The photograph is a close-up of the affected area; the lesion involves the back of the torso, arm, leg, head or neck and front of the torso:
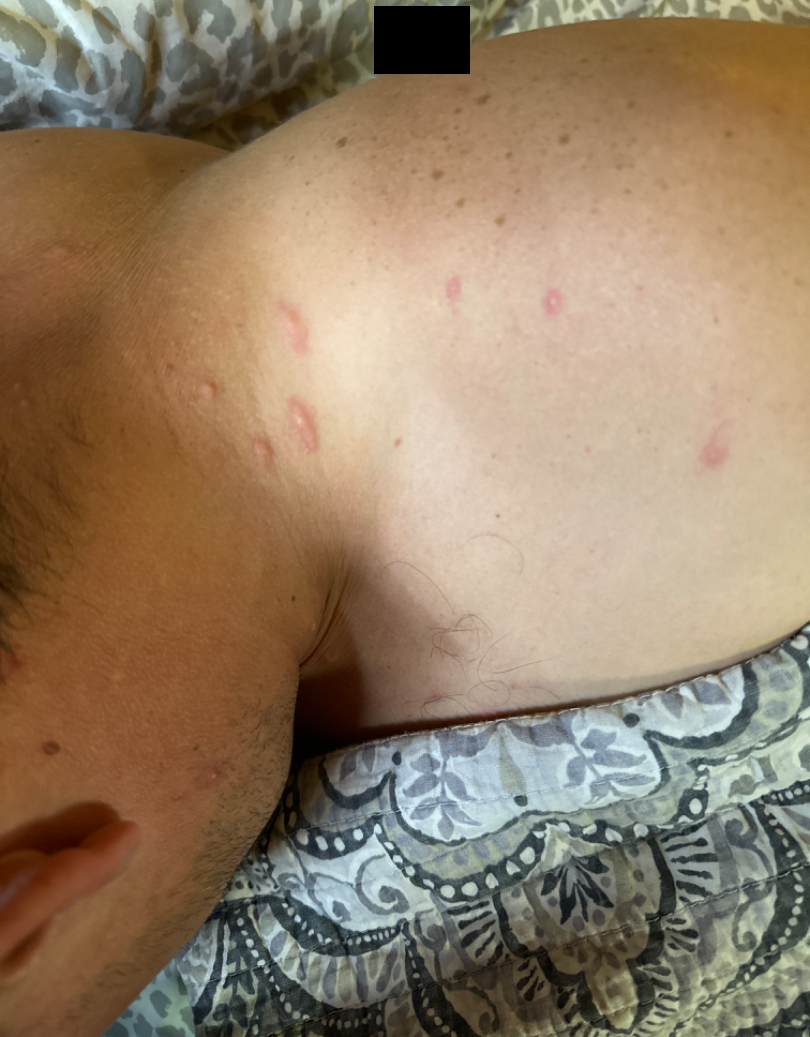lesion texture = fluid-filled
patient describes the issue as = a rash
skin tone = Fitzpatrick III; non-clinician graders estimated MST 3
dermatologist impression = reviewed remotely by one dermatologist: the leading consideration is Scar Condition; also on the differential is Folliculitis; also raised was Acne